Located on the head or neck · this is a close-up image · the condition has been present for one to four weeks · the subject is 18–29, female:
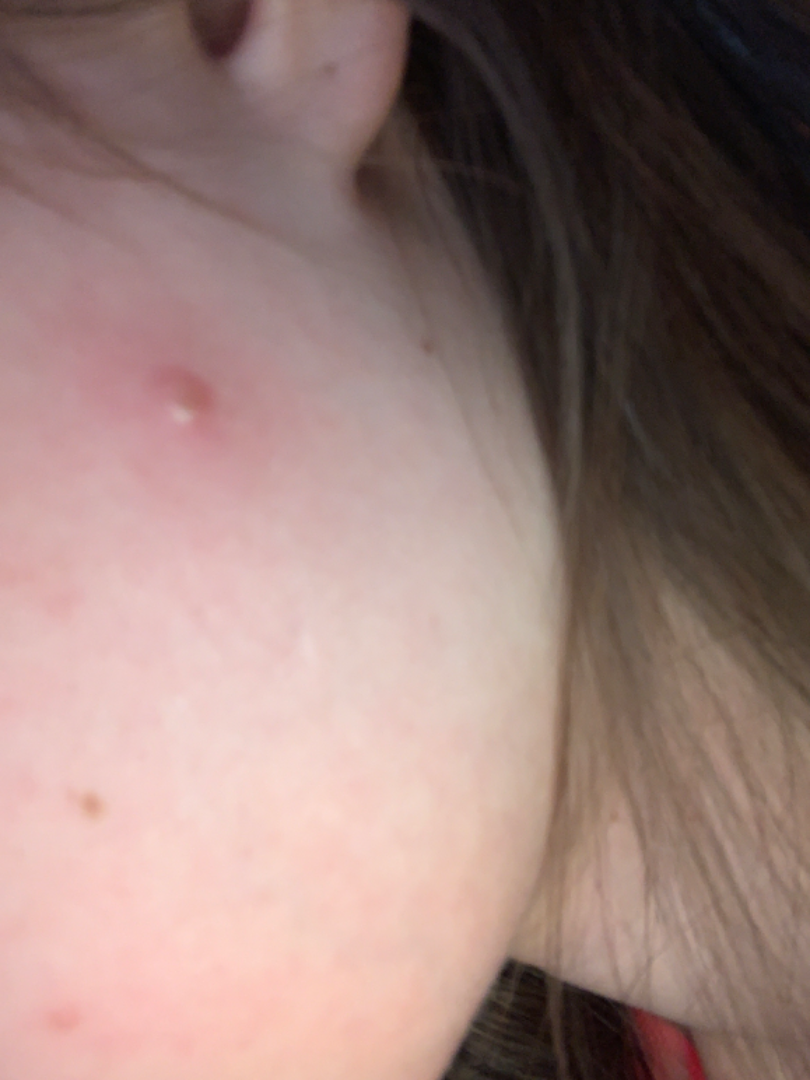The case was difficult to assess from the available photograph.